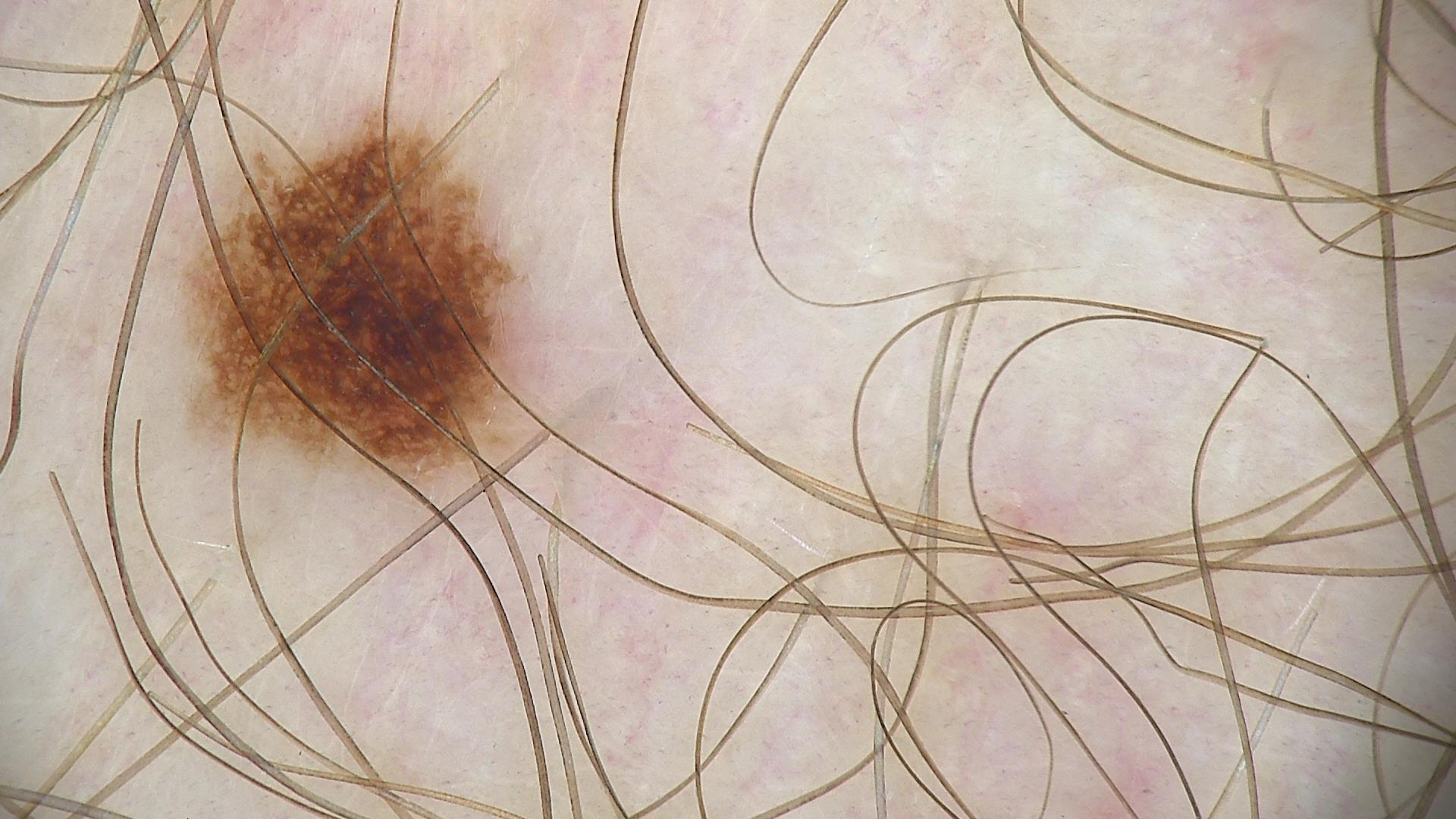image type: dermoscopy, diagnosis: dysplastic junctional nevus (expert consensus).